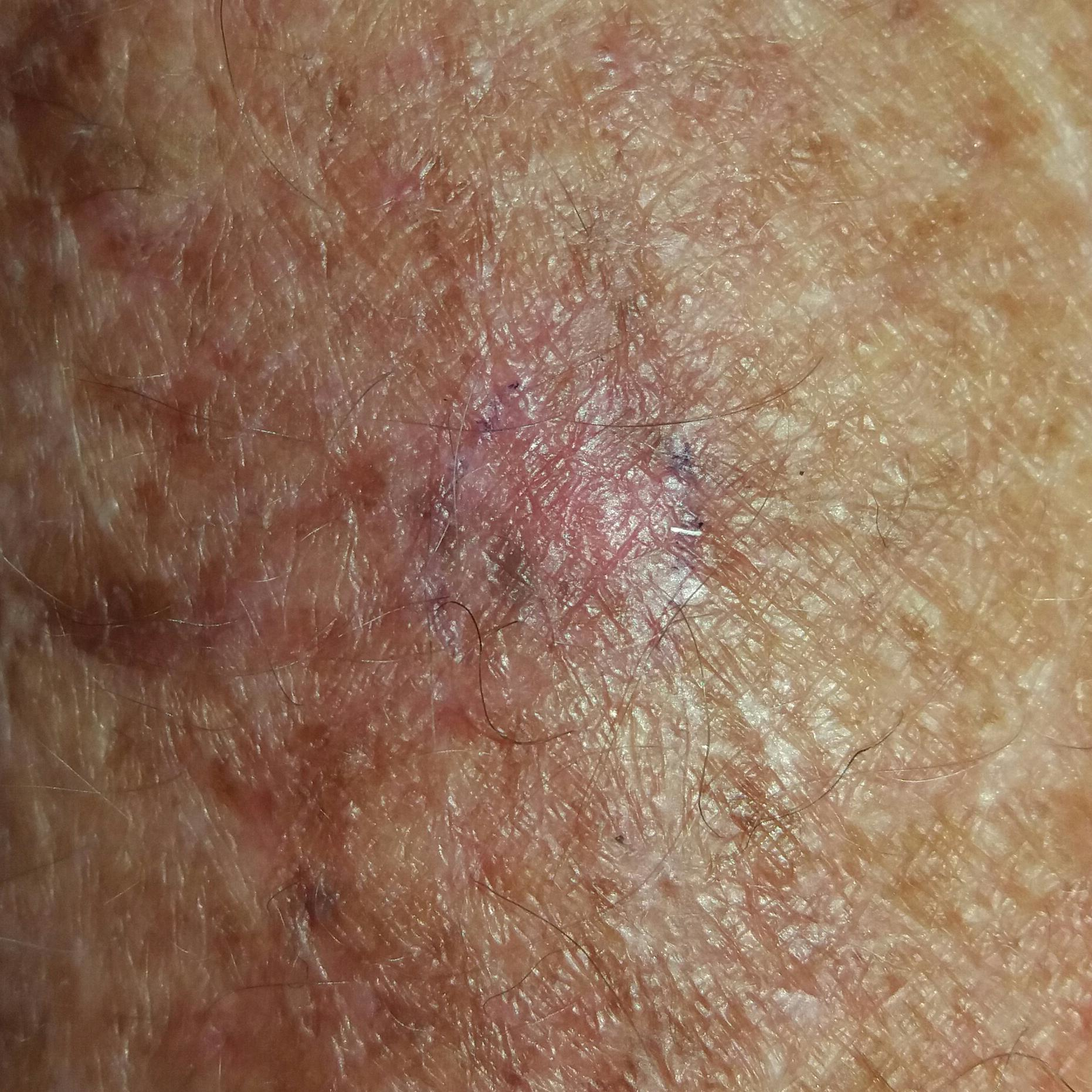  diagnosis:
    name: actinic keratosis
    code: ACK
    malignancy: indeterminate
    confirmation: clinical consensus